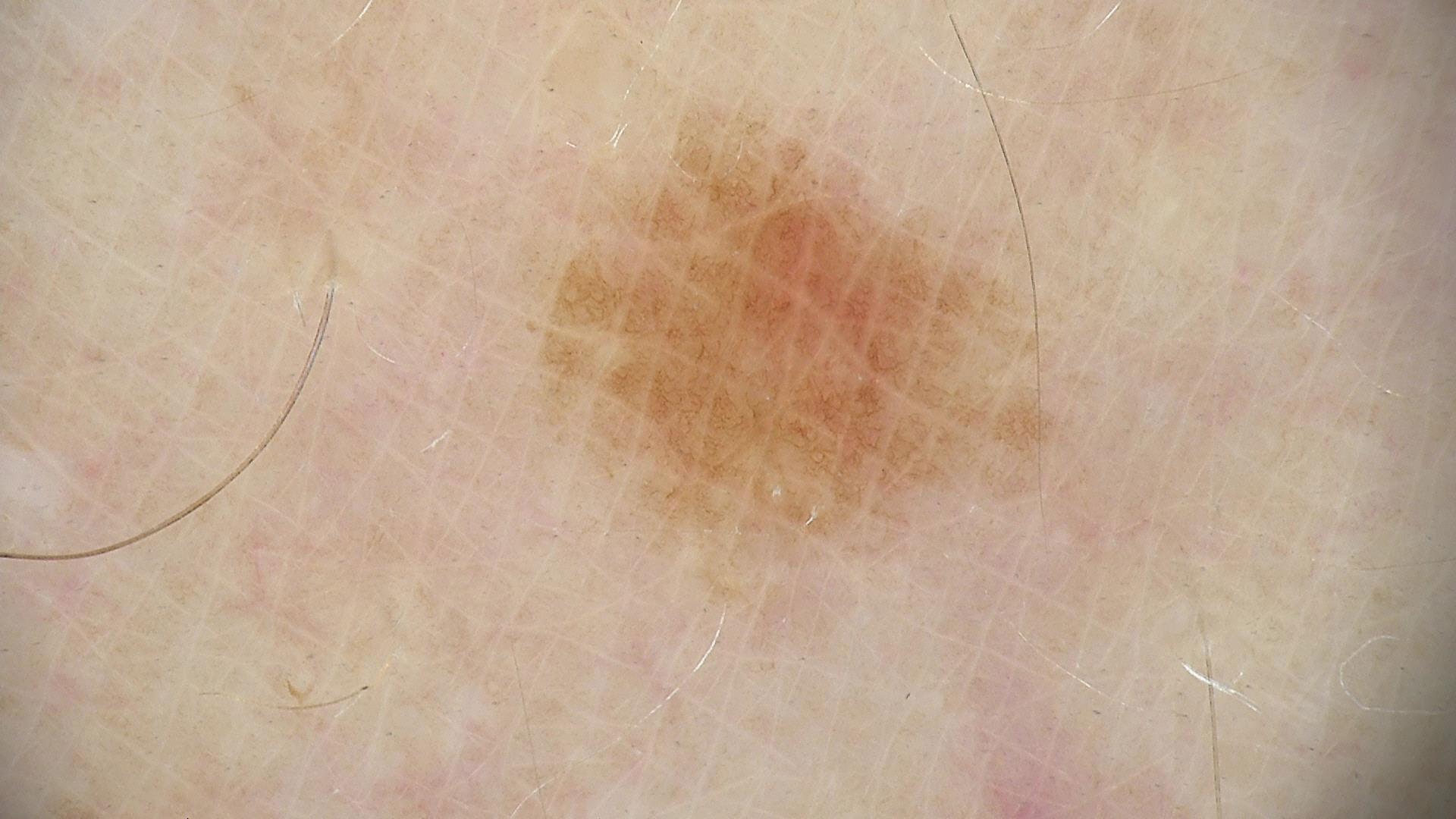Findings:
* assessment: solar lentigo (expert consensus)